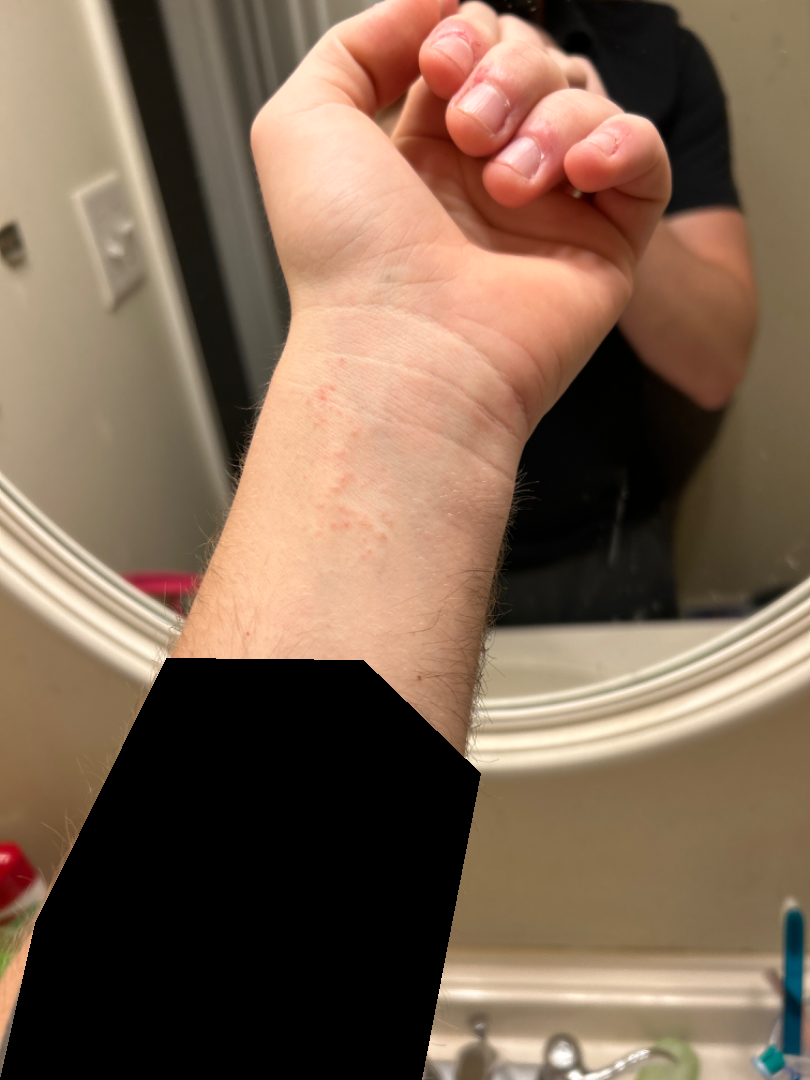Q: What was the assessment?
A: indeterminate from the photograph
Q: What is the affected area?
A: arm
Q: How does the patient describe it?
A: skin that appeared healthy to them
Q: What is the framing?
A: at a distance
Q: Reported symptoms?
A: itching
Q: How does the lesion feel?
A: raised or bumpy